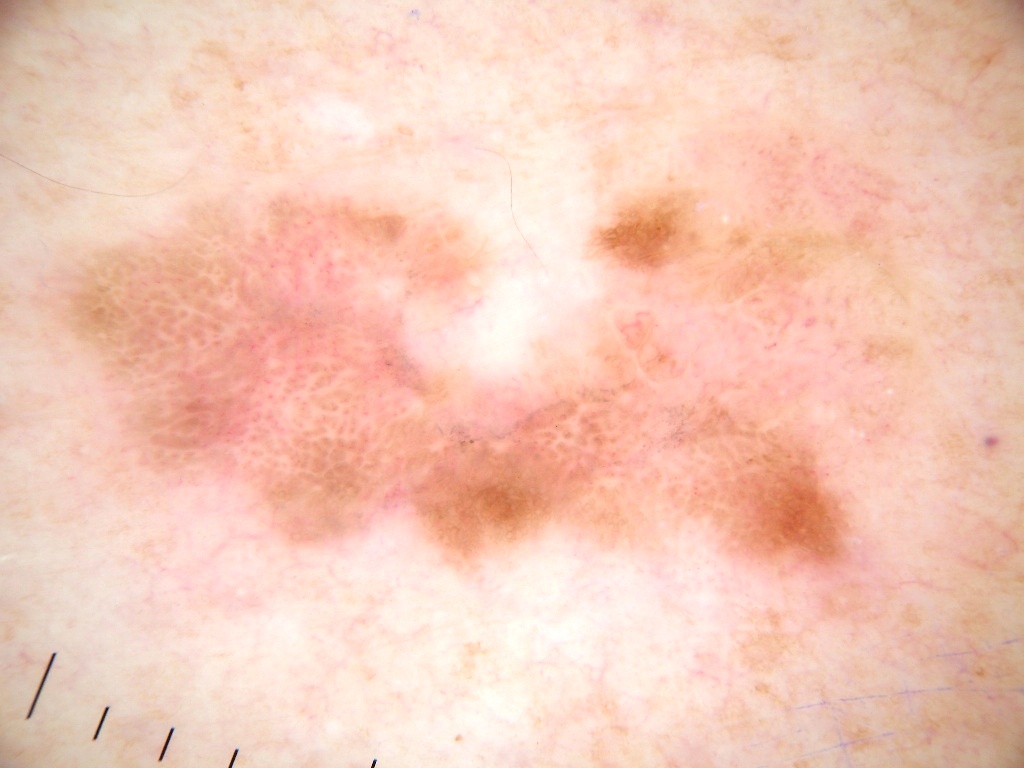A male patient, aged 73 to 77. A dermatoscopic image of a skin lesion. The dermoscopic pattern shows globules, milia-like cysts, negative network, and pigment network; no streaks. The lesion covers approximately 51% of the dermoscopic field. In (x1, y1, x2, y2) order, the lesion spans 18/113/935/651. Histopathology confirmed a melanoma, a malignant lesion.